An image taken at an angle. The affected area is the arm: 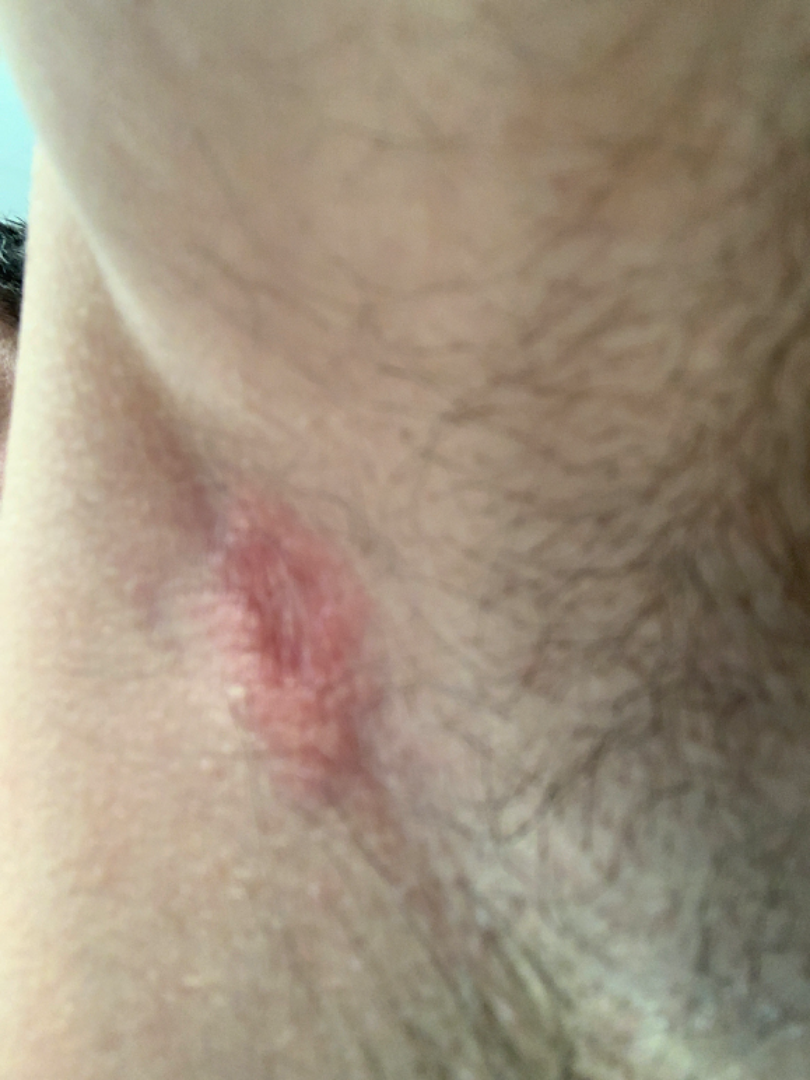<summary>
<assessment>not assessable</assessment>
</summary>